Located on the head or neck, the contributor reports the lesion is flat, the photograph is a close-up of the affected area, the patient considered this a rash.
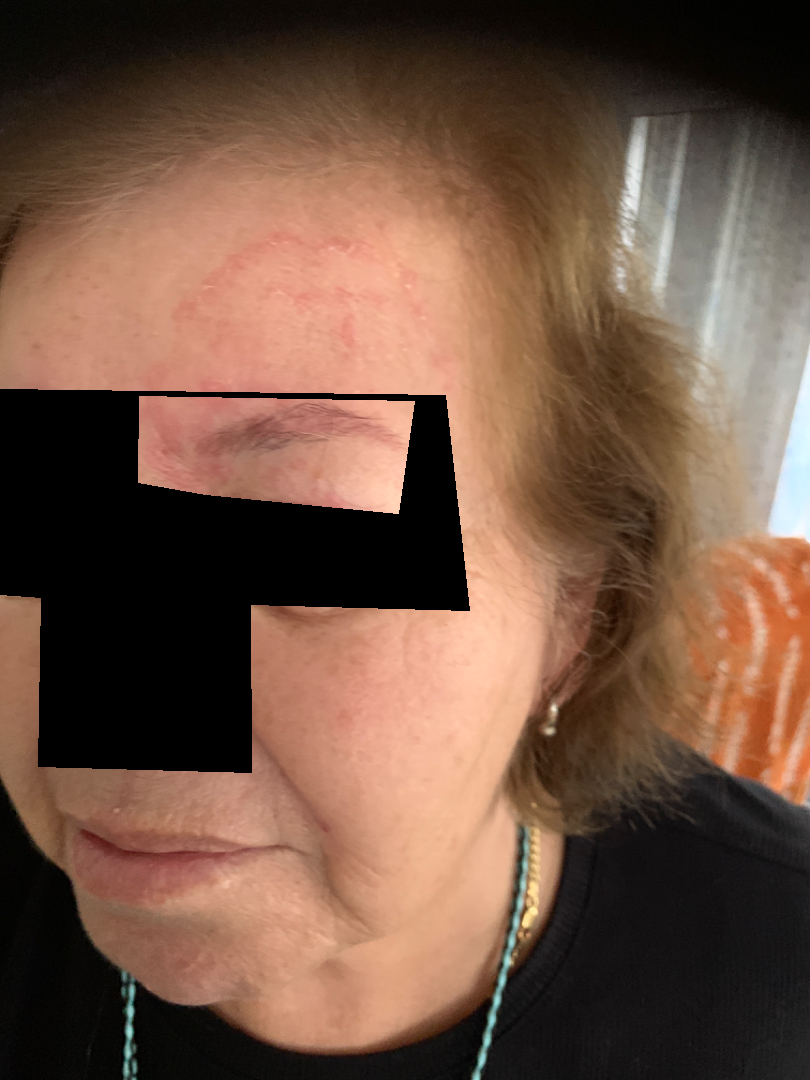| key | value |
|---|---|
| assessment | could not be assessed |